A dermoscopic close-up of a skin lesion.
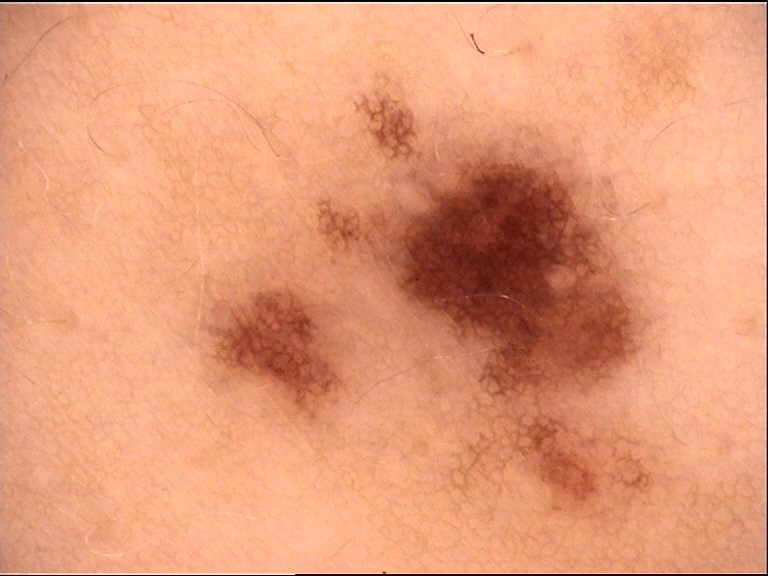label: dysplastic junctional nevus (expert consensus).